A dermoscopic close-up of a skin lesion: 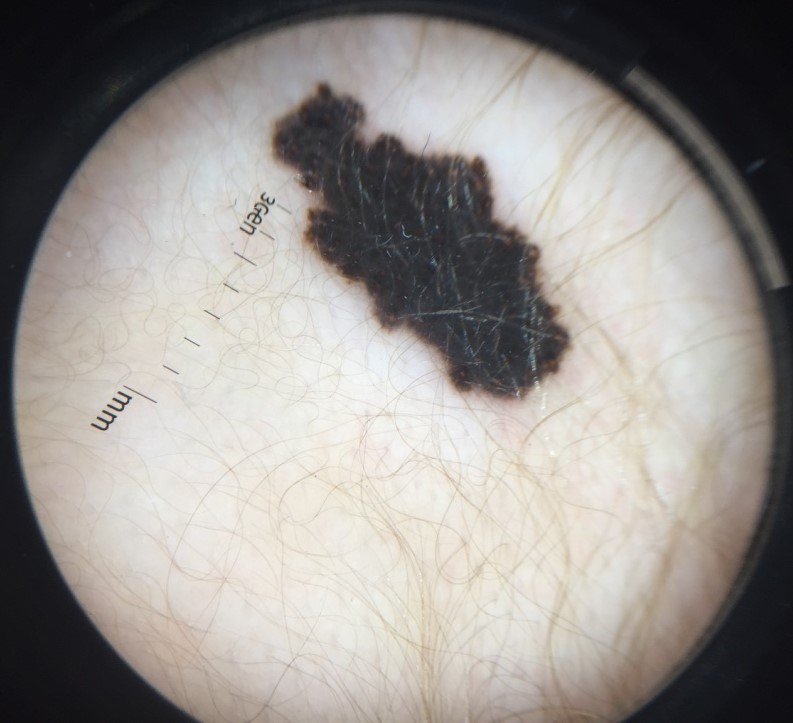<case>
<diagnosis>
<name>congenital compound nevus</name>
<code>ccb</code>
<malignancy>benign</malignancy>
<super_class>melanocytic</super_class>
<confirmation>expert consensus</confirmation>
</diagnosis>
</case>